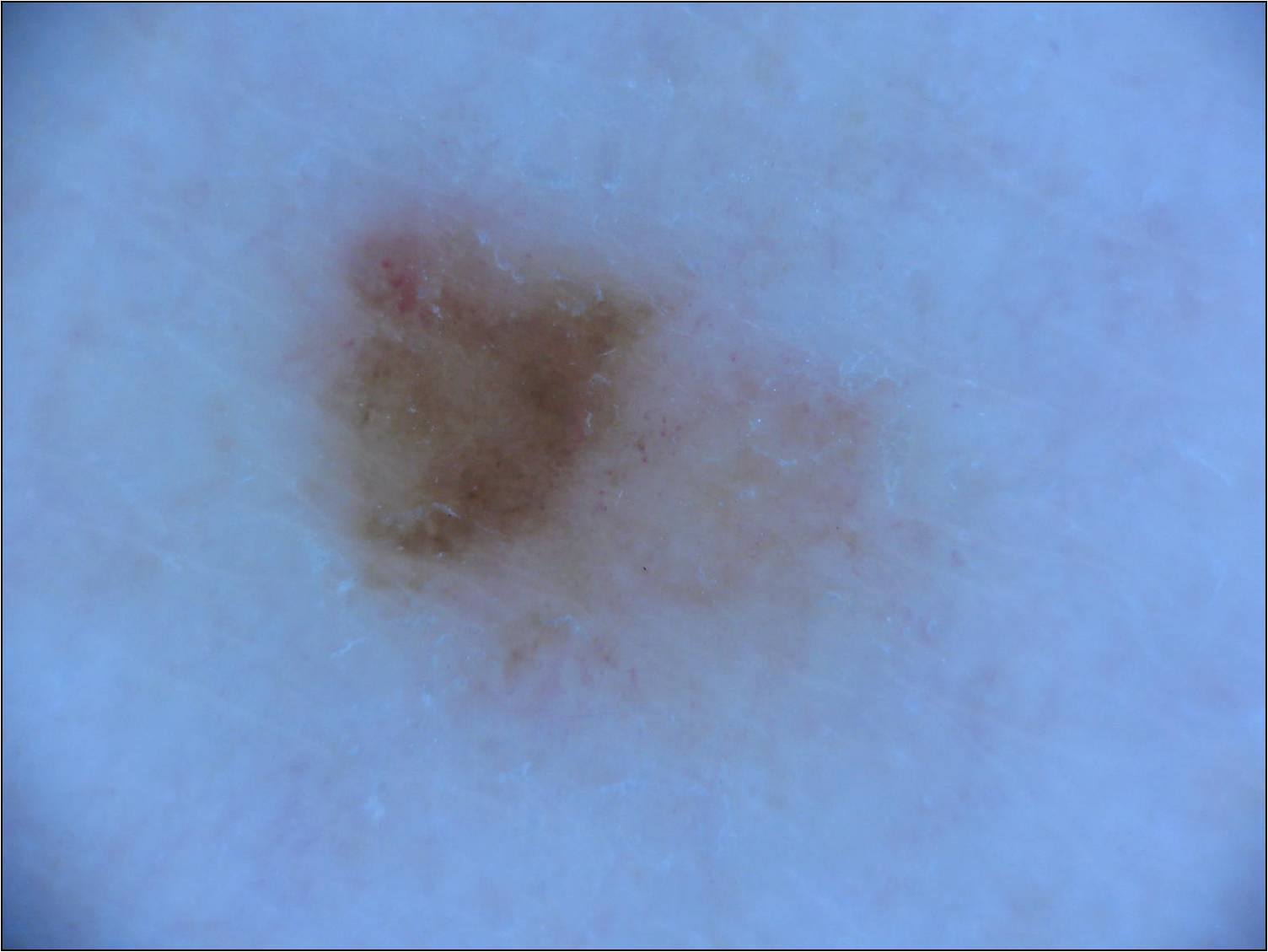Q: Patient demographics?
A: female, aged 63 to 67
Q: What is the imaging modality?
A: dermoscopic image
Q: Which dermoscopic features were noted?
A: globules; absent: streaks, milia-like cysts, pigment network, and negative network
Q: Where is the lesion located?
A: bbox=[282, 195, 873, 691]
Q: What did the assessment conclude?
A: a melanoma